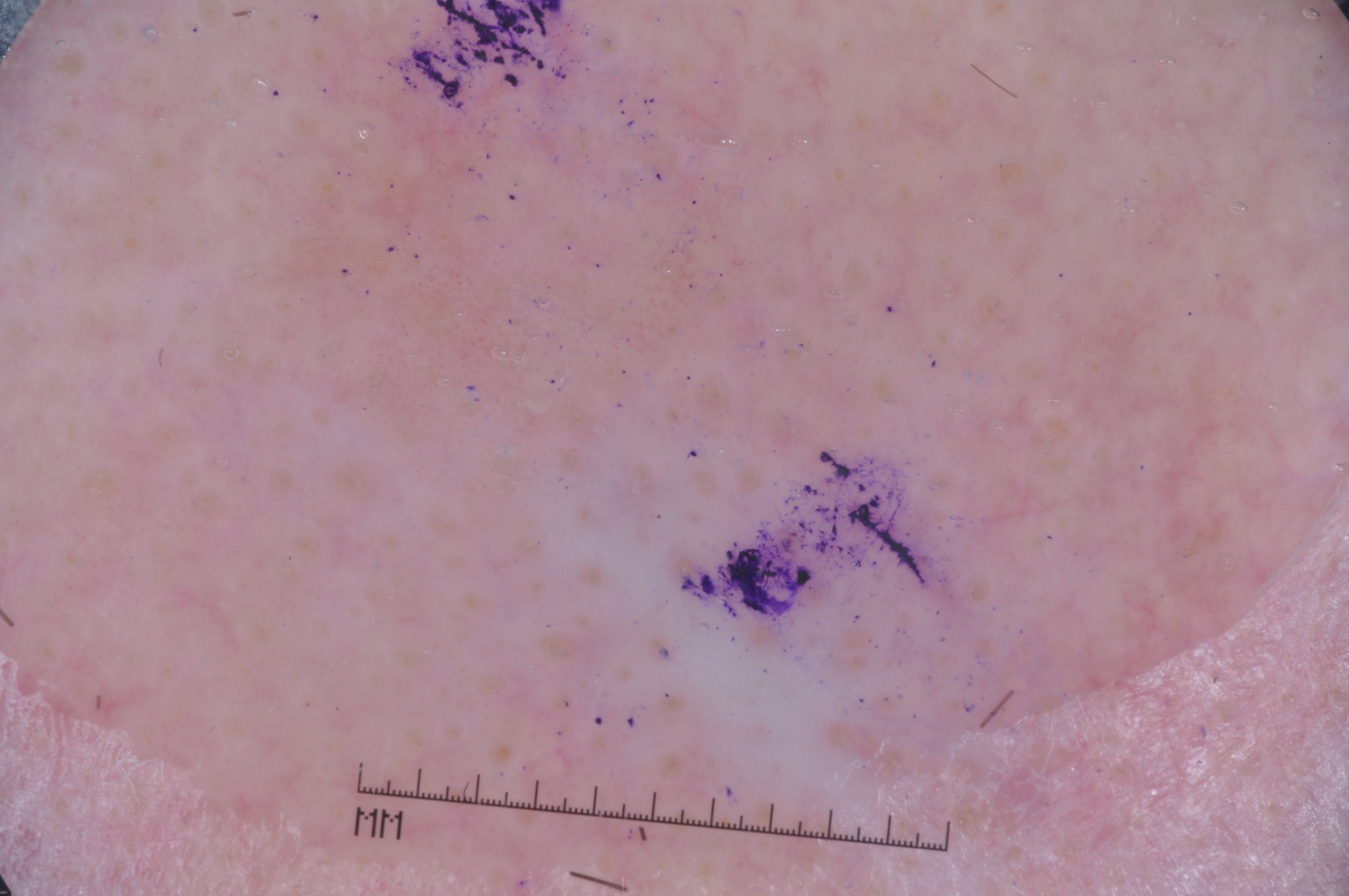  patient:
    sex: male
    age_approx: 70
  image:
    modality: dermoscopy
  lesion_location:
    bbox_xyxy:
      - 184
      - 6
      - 967
      - 740
  dermoscopic_features:
    present: []
    absent:
      - negative network
      - milia-like cysts
      - pigment network
      - streaks
  diagnosis:
    name: seborrheic keratosis
    malignancy: benign
    lineage: keratinocytic
    provenance: clinical